A female patient age 60; the patient says their skin tans without first burning; referred for assessment of suspected basal cell carcinoma; the patient describes having few moles overall:
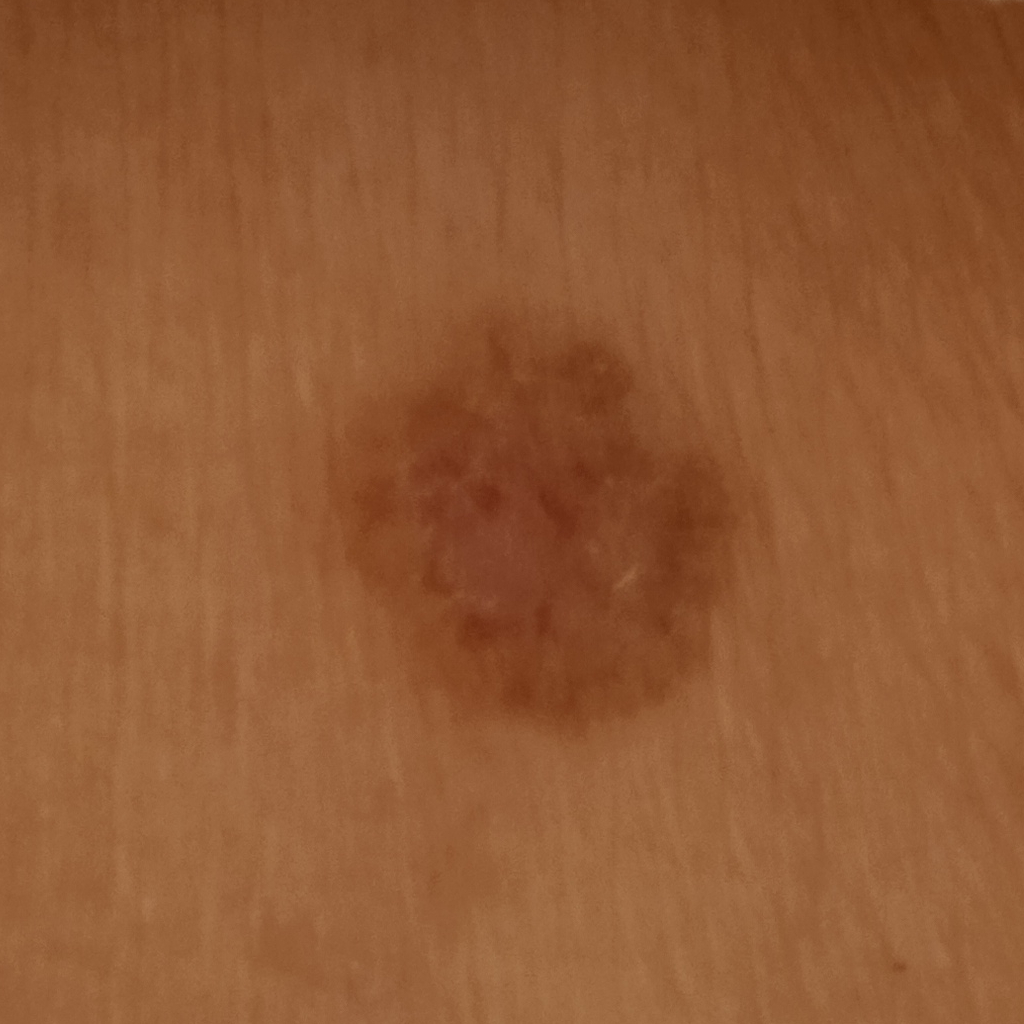Findings:
The lesion is on the torso.
Conclusion:
Dermatologist review favored a basal cell carcinoma.